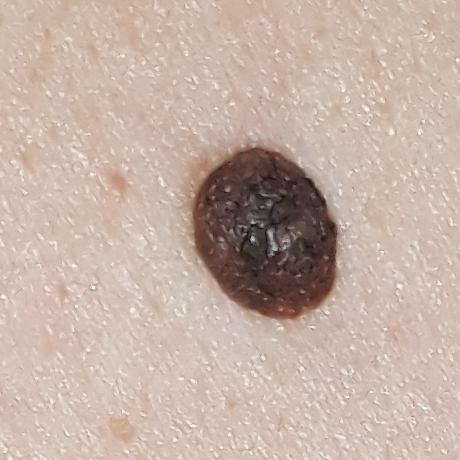{"patient": {"age": 35}, "lesion_location": "the back", "symptoms": {"present": ["elevation"]}, "diagnosis": {"name": "nevus", "code": "NEV", "malignancy": "benign", "confirmation": "clinical consensus"}}